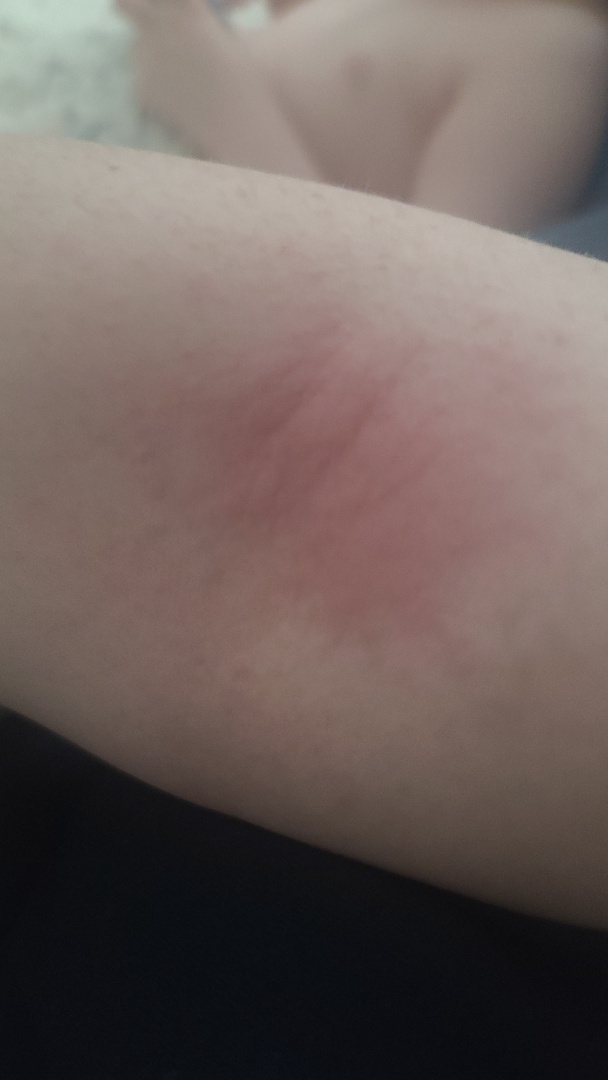Patient information:
The contributor is a female aged 30–39. The photograph is a close-up of the affected area. The lesion involves the arm.
Review:
Most consistent with Eczema.